A female subject 55 years of age. Collected as part of a research study, without a referral diagnosis.
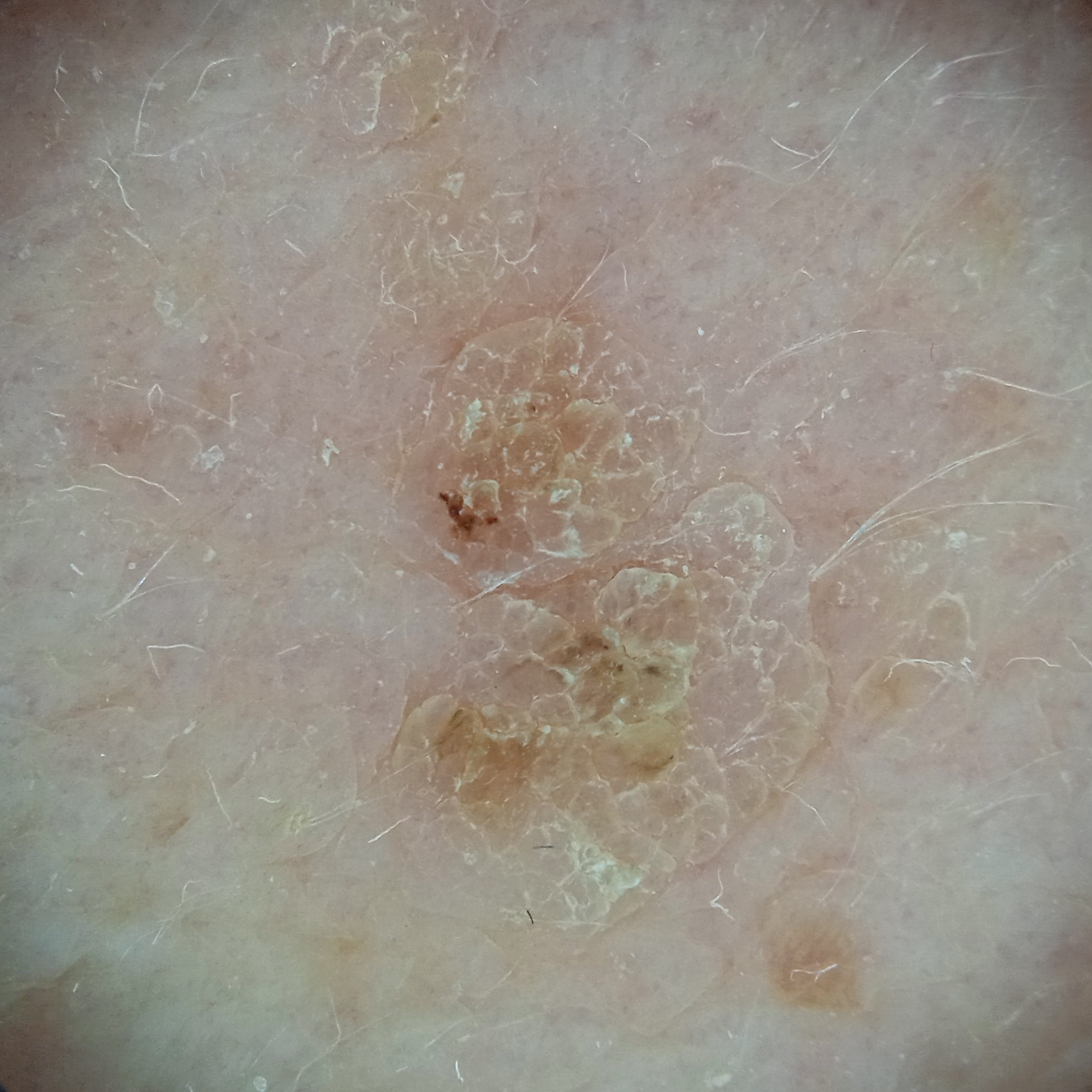{
  "lesion_location": "the back",
  "lesion_size": {
    "diameter_mm": 10.6
  },
  "diagnosis": {
    "name": "seborrheic keratosis",
    "malignancy": "benign"
  }
}